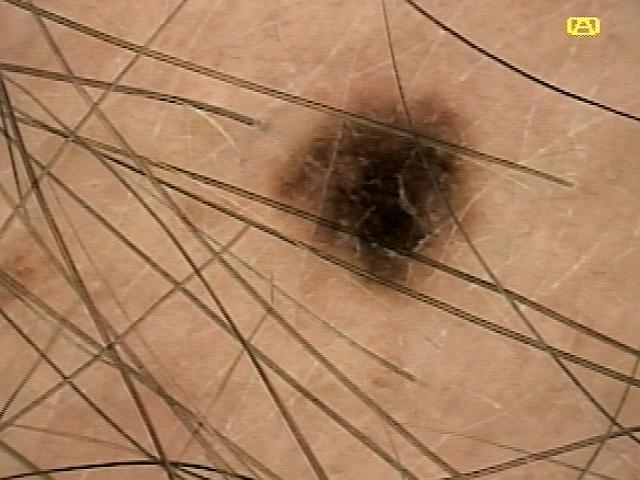Recorded as Fitzpatrick skin type II.
A dermoscopic image of a skin lesion.
Per the chart, no melanoma in first-degree relatives and no previous melanoma.
A male patient aged 43-47.
Located on a lower extremity.
Histopathology confirmed a benign lesion — a nevus.